The subject is a female aged 18–29, no relevant systemic symptoms, the affected area is the arm, self-categorized by the patient as a rash, the contributor reports the condition has been present for less than one week, a close-up photograph, the contributor reports the lesion is raised or bumpy, the lesion is associated with itching — 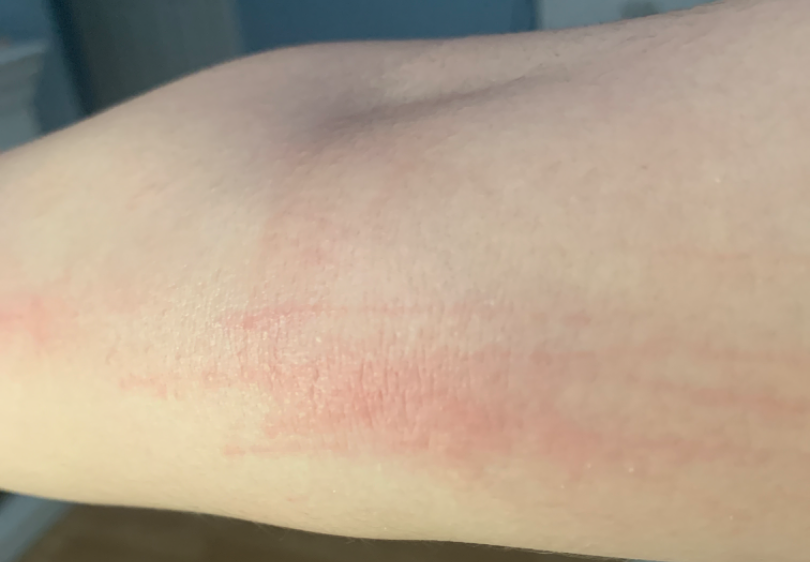  differential:
    Urticaria: 1.0